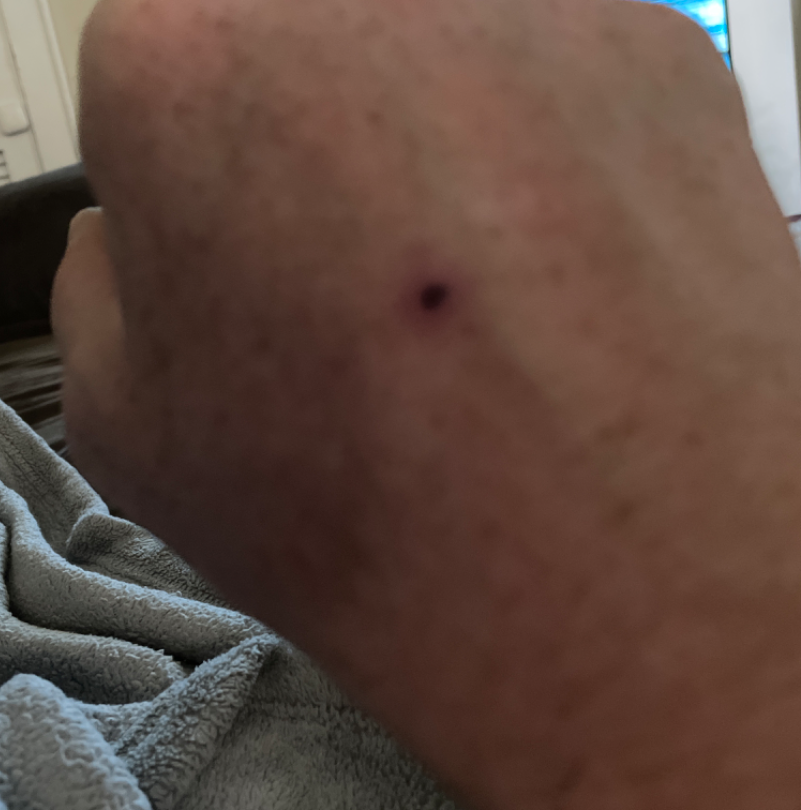Findings:
No differential diagnosis could be assigned on photographic review.
Background:
An image taken at an angle. The condition has been present for one to four weeks. The back of the hand, leg, head or neck and arm are involved. The patient notes associated fatigue. Male patient, age 40–49. The lesion is described as flat.